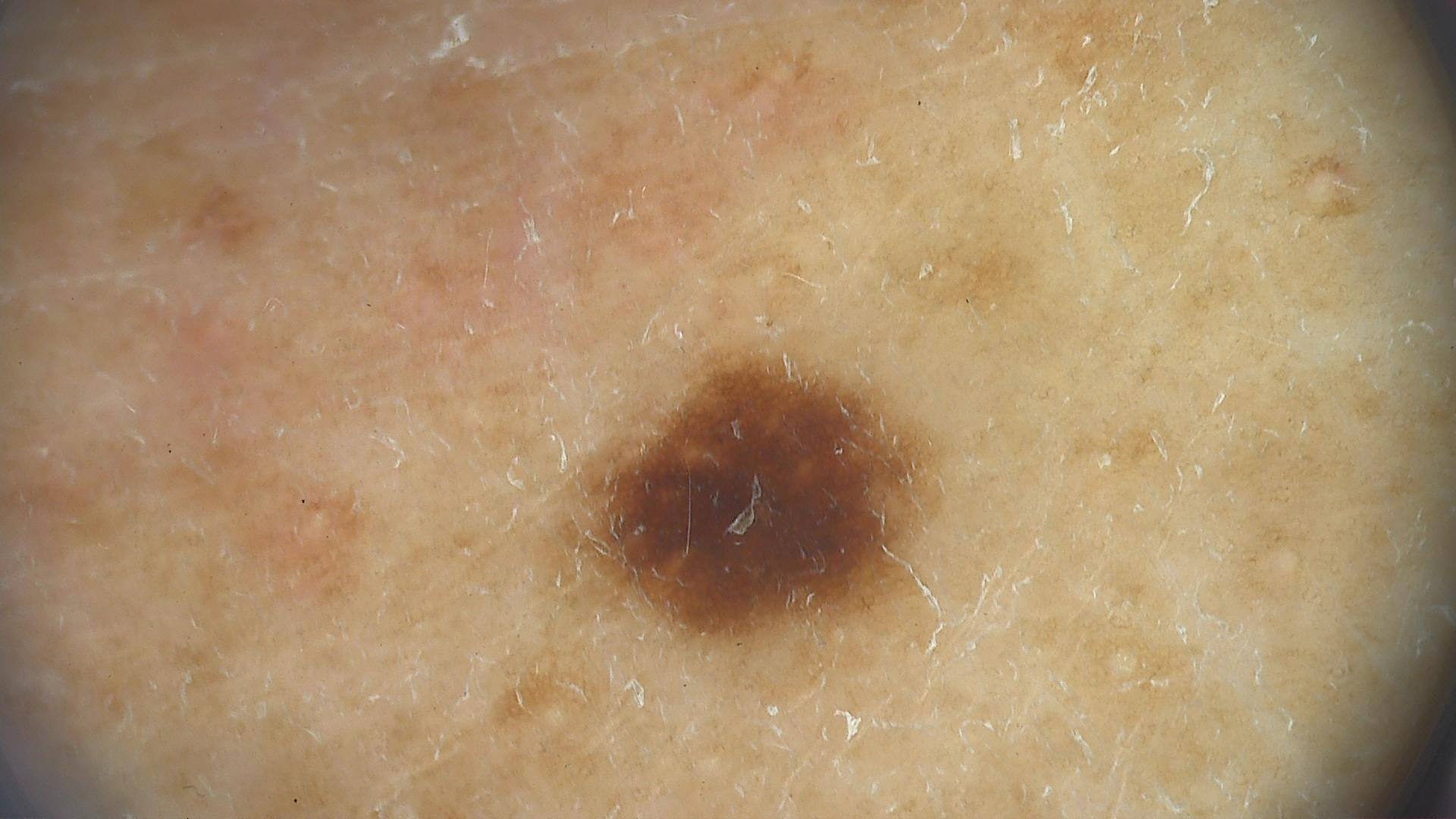| key | value |
|---|---|
| diagnosis | dysplastic junctional nevus (expert consensus) |